The patient considered this a rash. Associated systemic symptoms include fatigue. Texture is reported as raised or bumpy and fluid-filled. Reported duration is one to four weeks. The contributor is a female aged 18–29. Reported lesion symptoms include bothersome appearance, enlargement, pain and itching. The photo was captured at an angle. The affected area is the back of the hand: 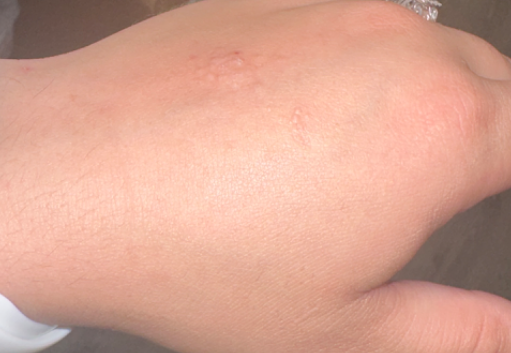On remote dermatologist review: most likely Contact dermatitis; an alternative is Lichen nitidus; also on the differential is Eczema; also consider Allergic Contact Dermatitis.